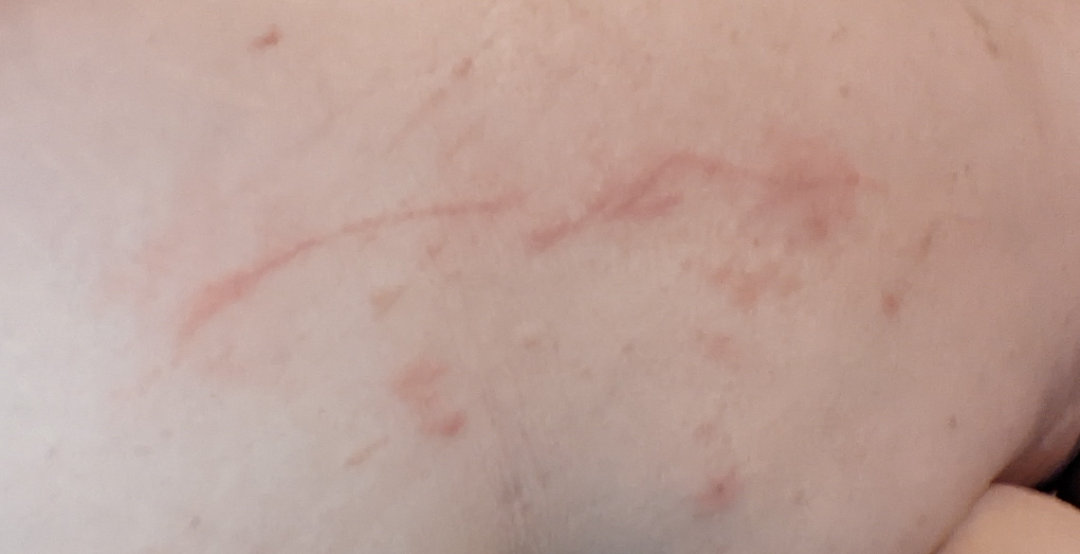Findings: On independent review by the dermatologists, most consistent with Hypersensitivity; also on the differential is Eczema; with consideration of Allergic Contact Dermatitis; less likely is Inflicted skin lesions; less probable is Urticaria; a remote consideration is Flagellate erythema.